The lesion involves the arm. Close-up view: 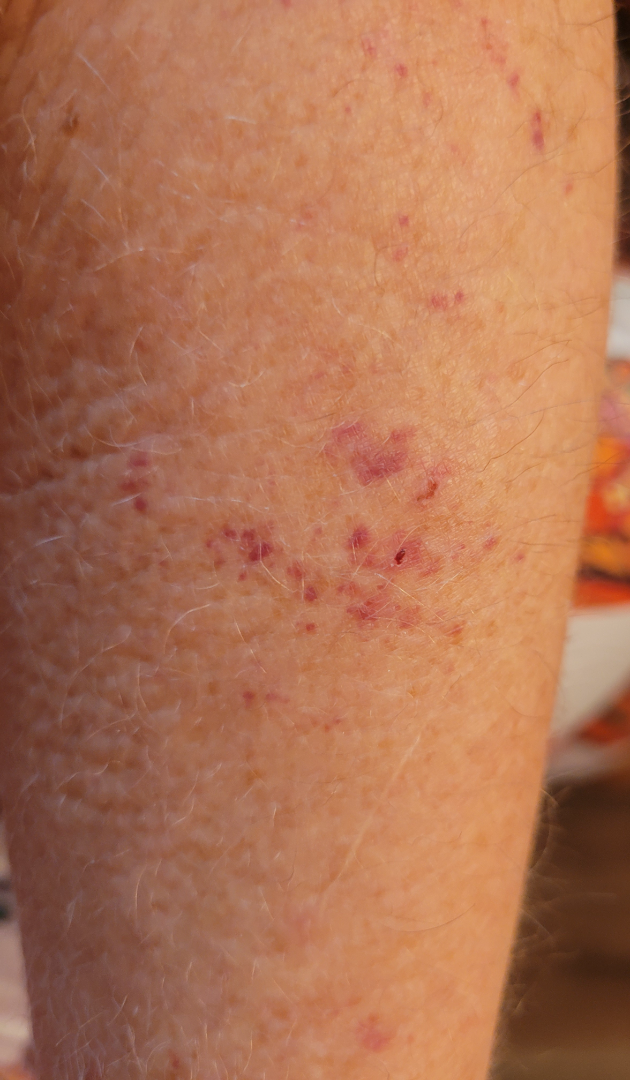Q: Could the case be diagnosed?
A: not assessable